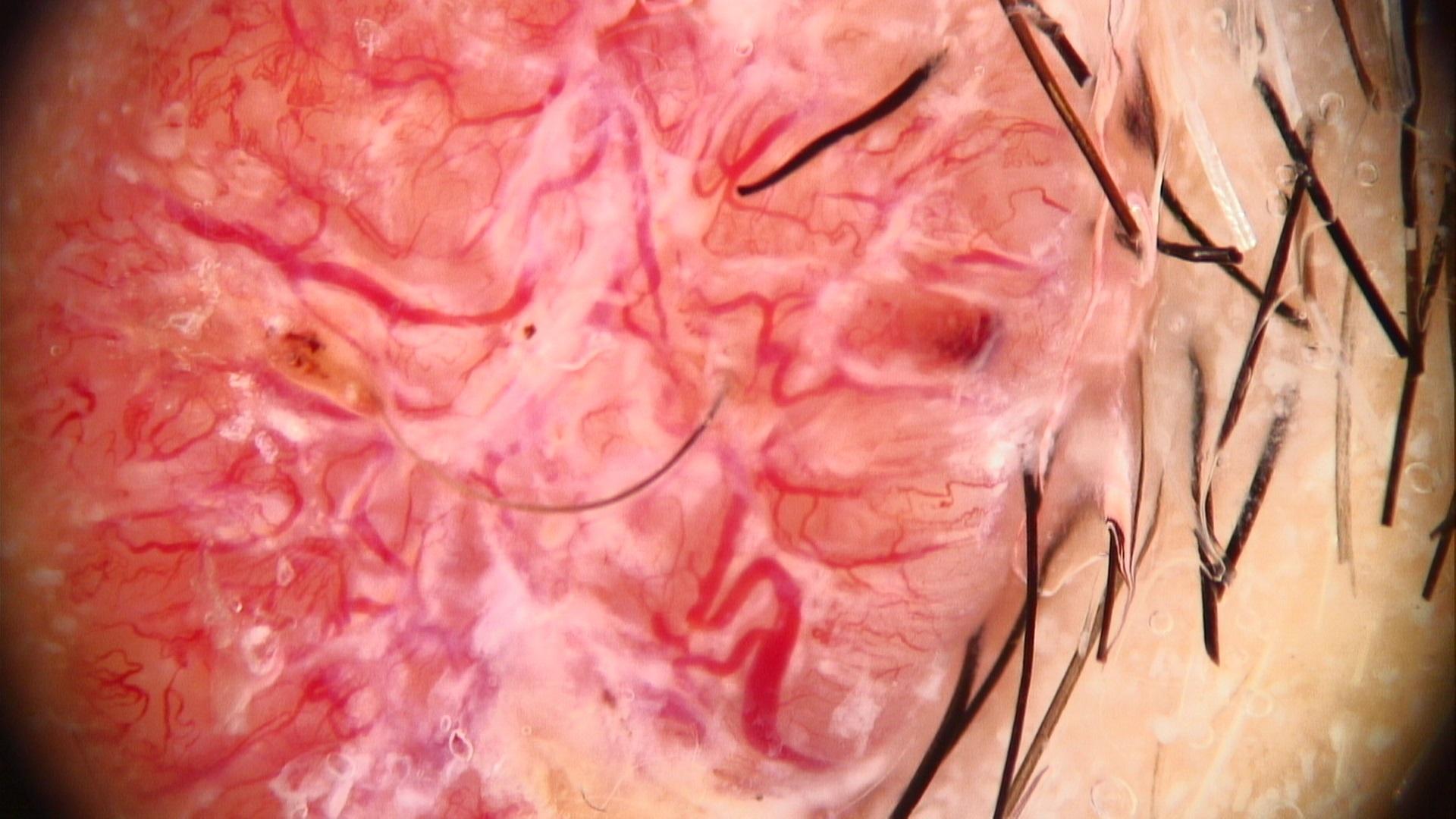patient: male | image: dermatoscopic image | site: the head or neck | diagnostic label: Basal cell carcinoma (biopsy-proven).